Dermoscopy of a skin lesion.
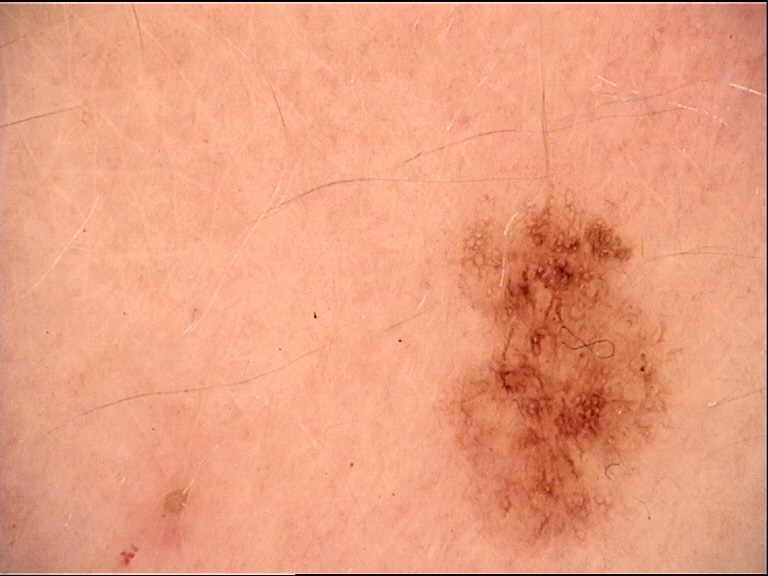Diagnosed as a dysplastic junctional nevus.